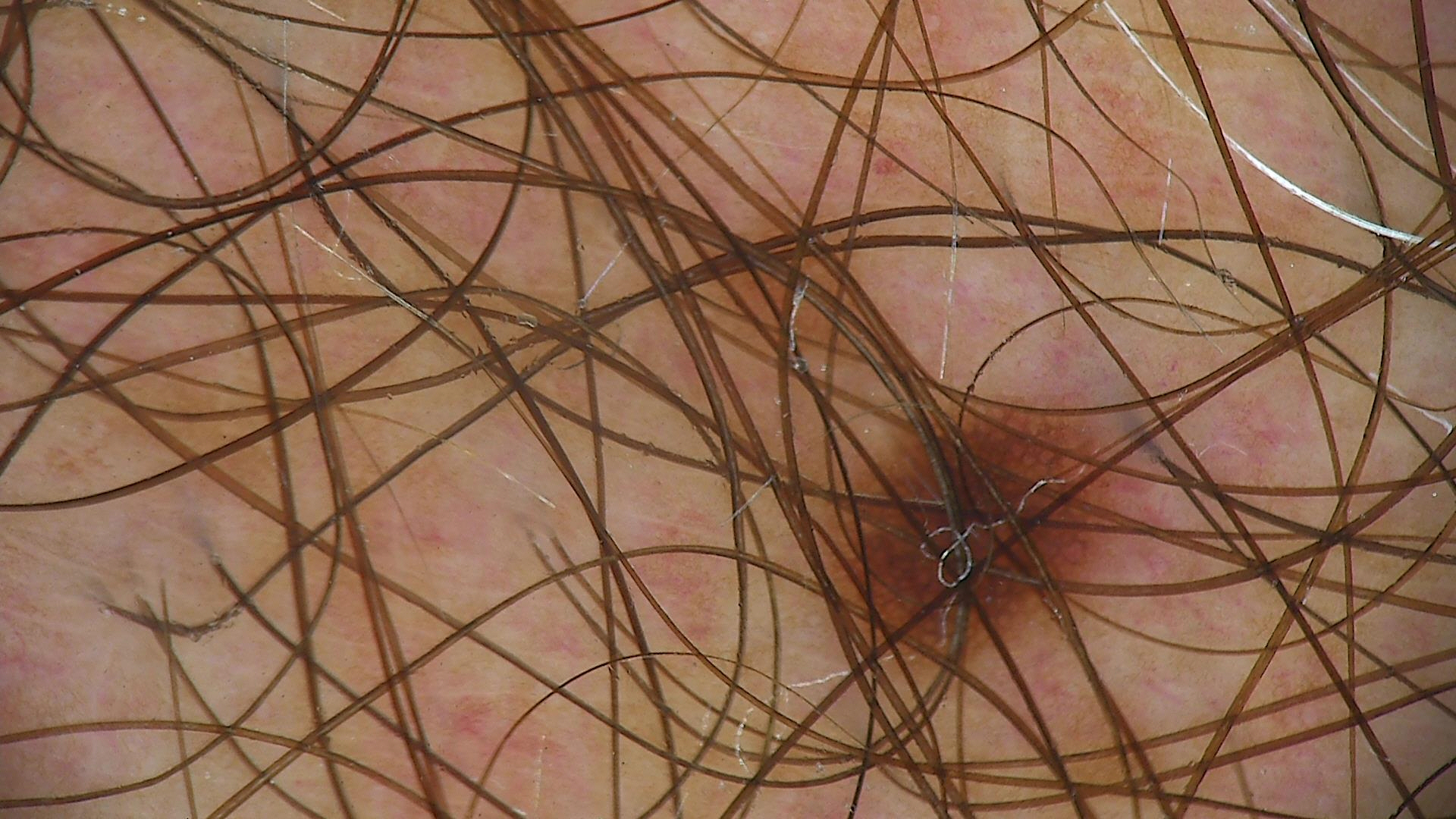Classified as a banal lesion — a junctional nevus.